The photograph was taken at a distance · the subject is female · located on the sole of the foot and top or side of the foot:
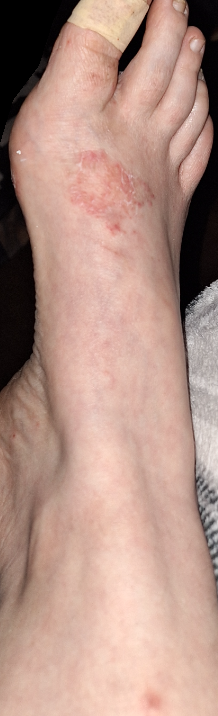Findings:
• diagnostic considerations · most consistent with Tinea; possibly Psoriasis; also raised was Eczema